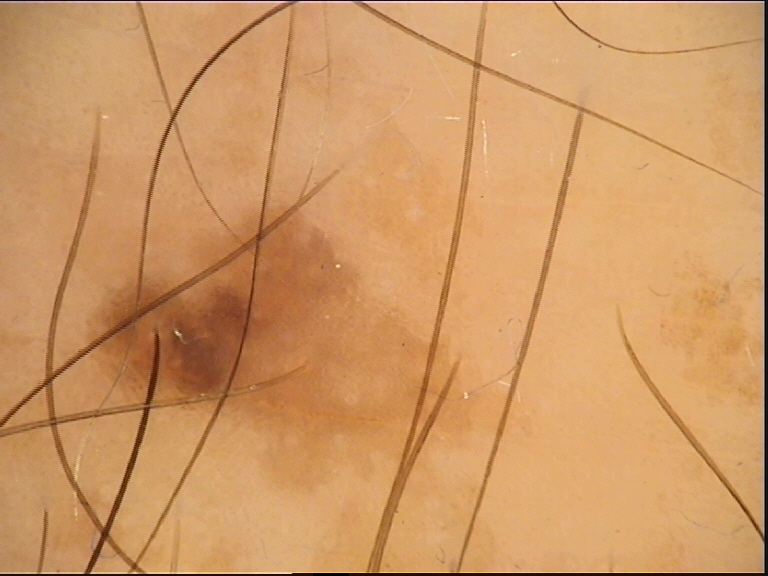| key | value |
|---|---|
| imaging | dermoscopy |
| assessment | dysplastic junctional nevus (expert consensus) |